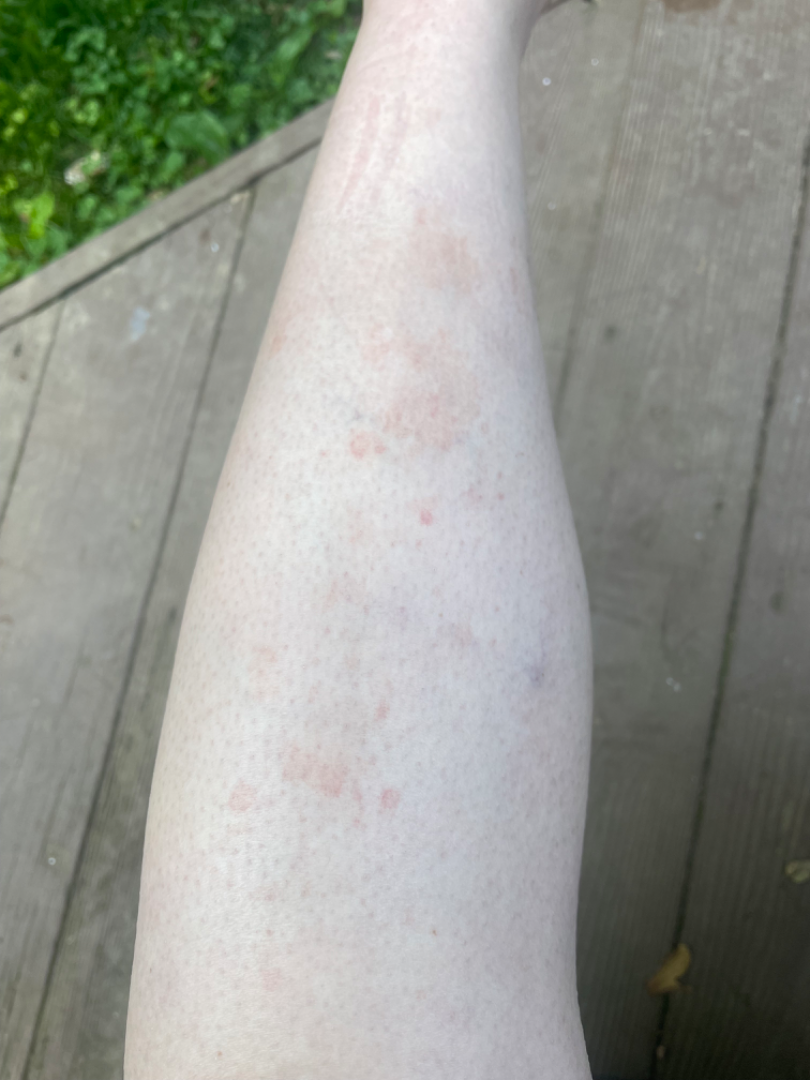Impression:
The case was difficult to assess from the available photograph.